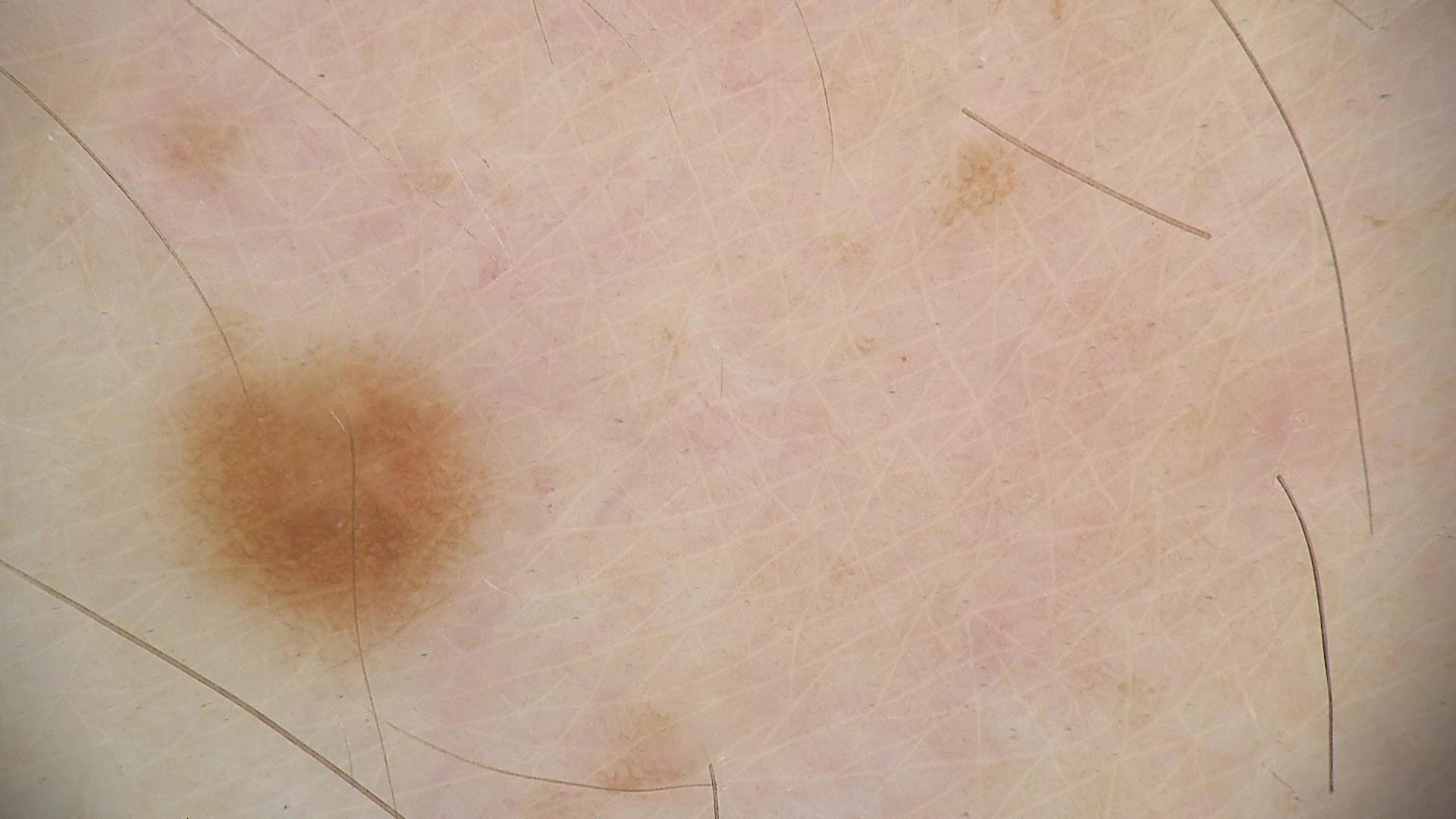image: dermatoscopy | label: dysplastic junctional nevus (expert consensus).